A clinical photograph showing a skin lesion. A moderate number of moles by the patient's own estimate. The patient says their skin tans without first burning. A male subject 72 years of age.
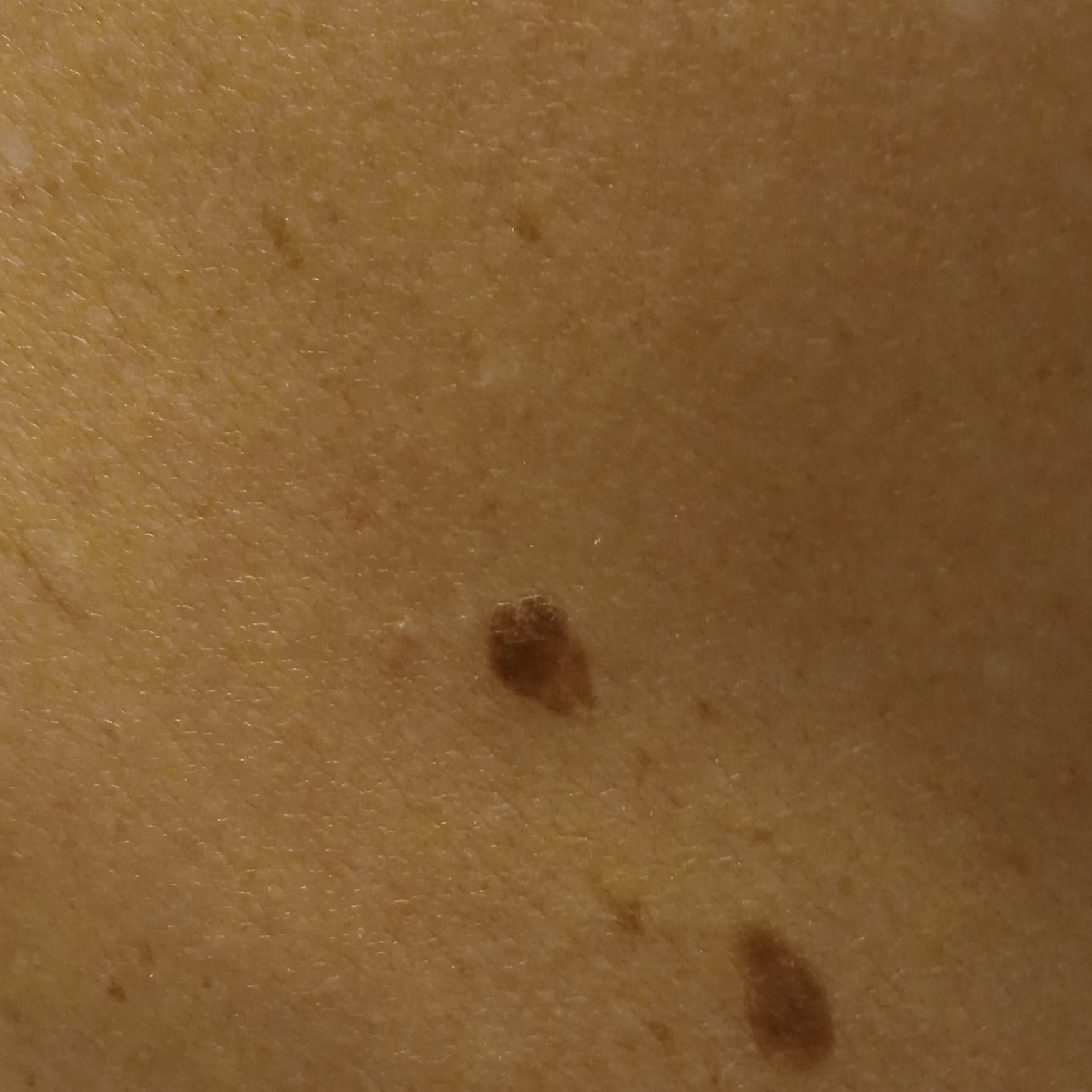<case>
<lesion_location>the back</lesion_location>
<lesion_size>
<diameter_mm>9.6</diameter_mm>
</lesion_size>
<diagnosis>
<name>seborrheic keratosis</name>
<malignancy>benign</malignancy>
</diagnosis>
</case>